An image taken at an angle · the back of the torso is involved · the patient is a female aged 18–29: 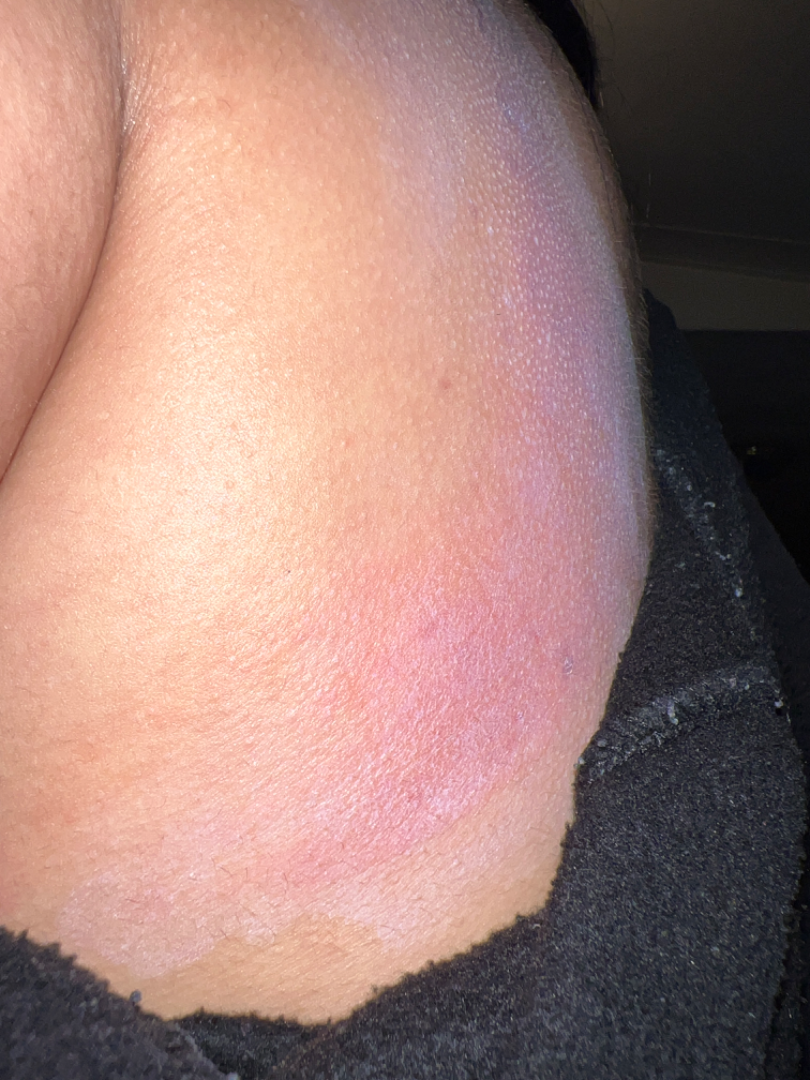| field | value |
|---|---|
| assessment | indeterminate from the photograph |